A dermoscopic image of a skin lesion.
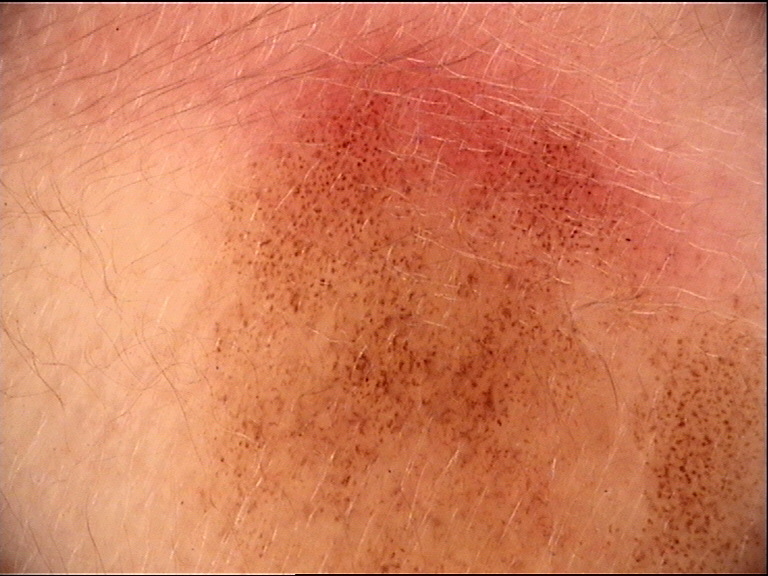Q: What is this lesion?
A: congenital junctional nevus (expert consensus)